The lesion involves the arm; the photo was captured at an angle; the contributor is 50–59, female: 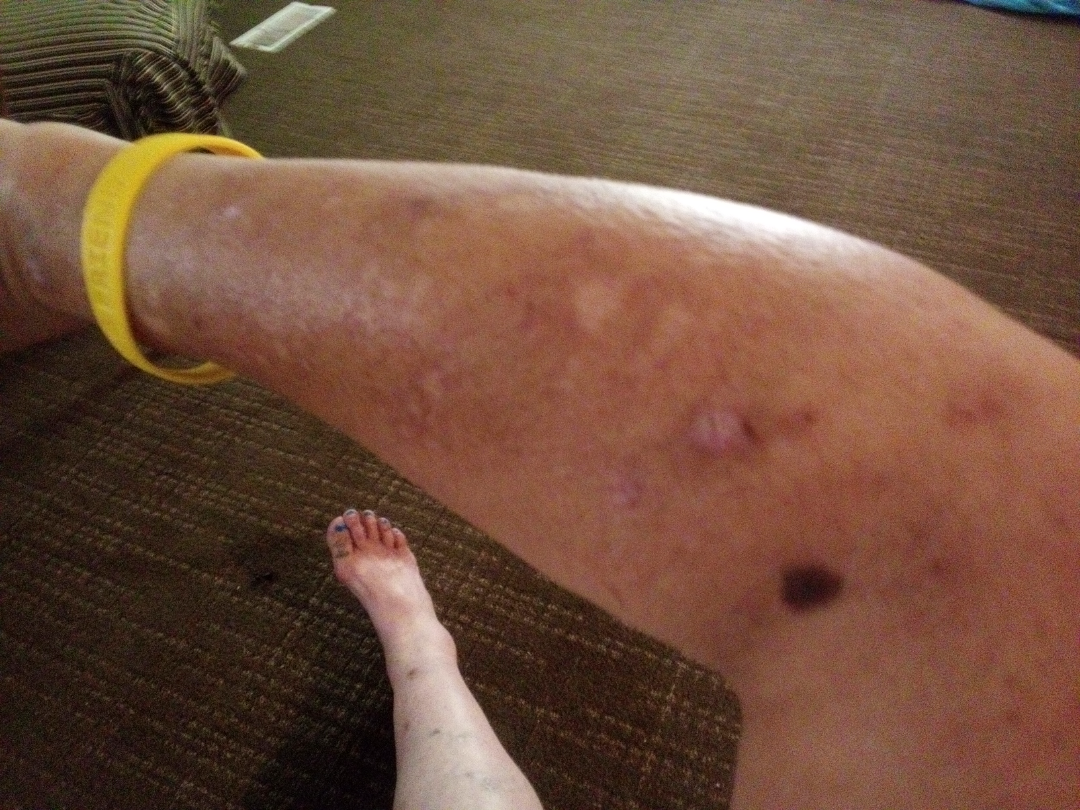assessment = indeterminate.